A dermoscopy image of a single skin lesion: 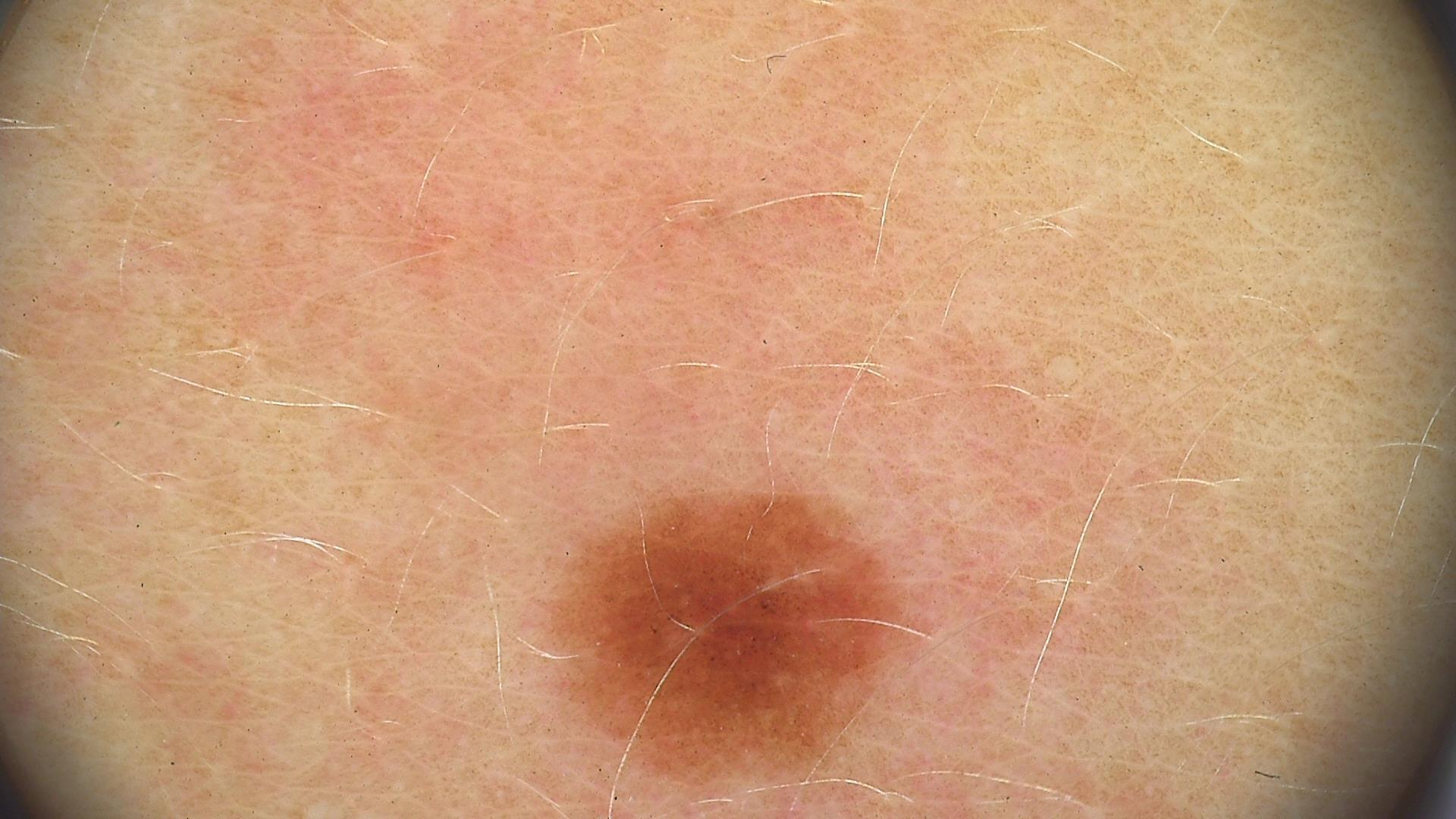The diagnostic label was a benign lesion — a dysplastic junctional nevus.